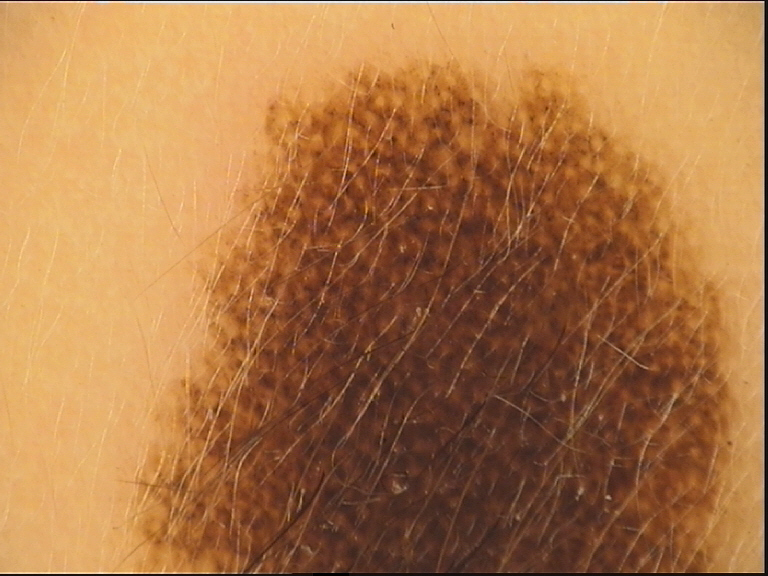Findings:
- modality: dermoscopy
- classification: banal
- label: congenital compound nevus (expert consensus)